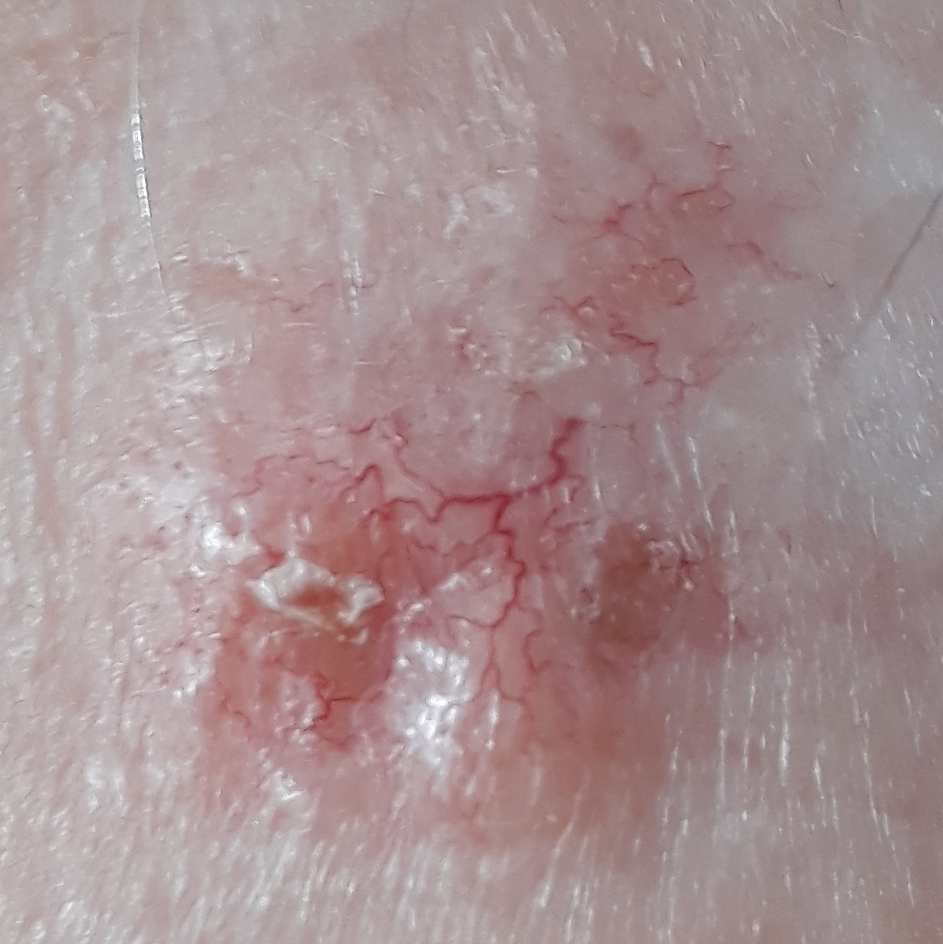Pathology: The biopsy diagnosis was a basal cell carcinoma.